This is a close-up image — 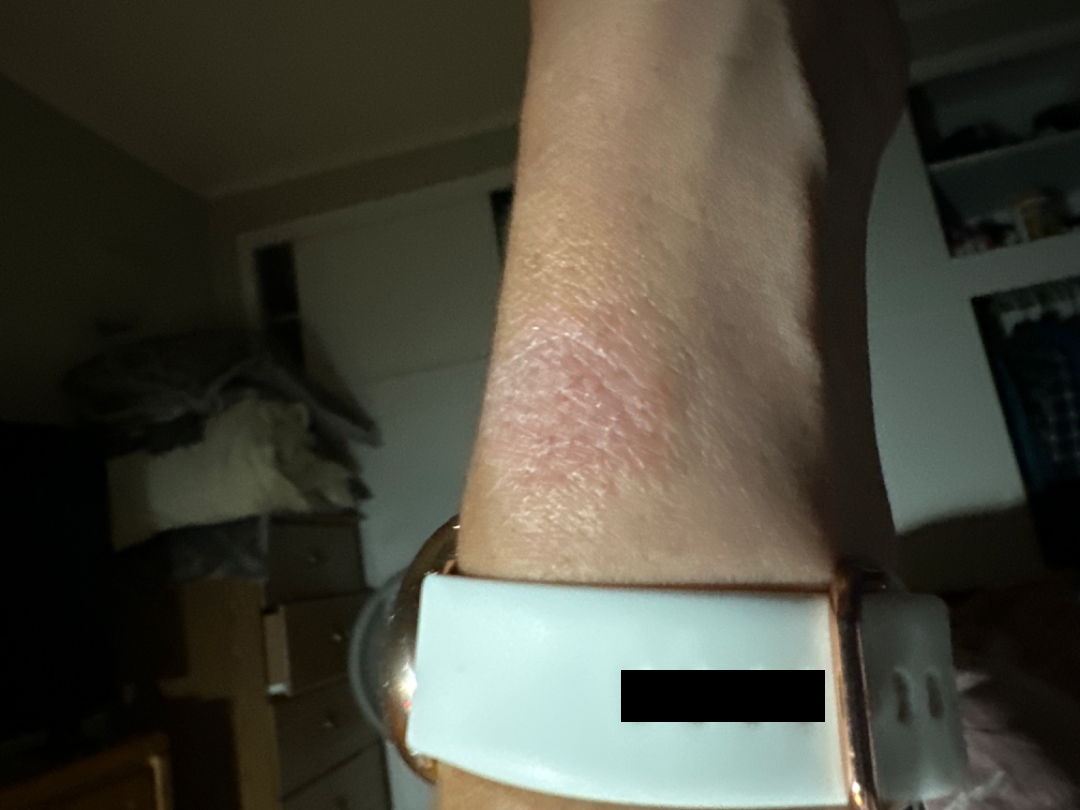Patient information: Skin tone: Fitzpatrick skin type III. Review: Allergic Contact Dermatitis and Irritant Contact Dermatitis were each considered, in no particular order.